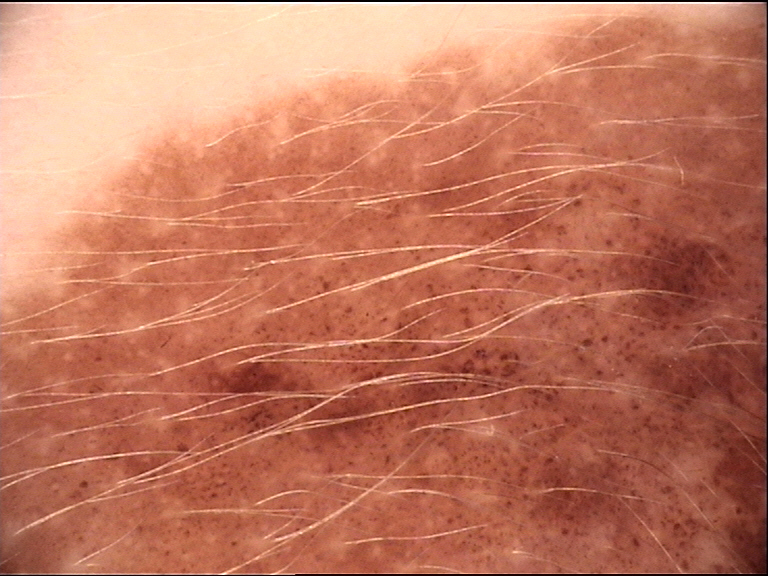Summary: A dermatoscopic image of a skin lesion. The architecture is that of a banal lesion. Conclusion: Diagnosed as a congenital junctional nevus.